The head or neck, back of the torso, arm and front of the torso are involved; no constitutional symptoms were reported; the patient considered this skin that appeared healthy to them; the contributor notes itching; the condition has been present for less than one week; close-up view.
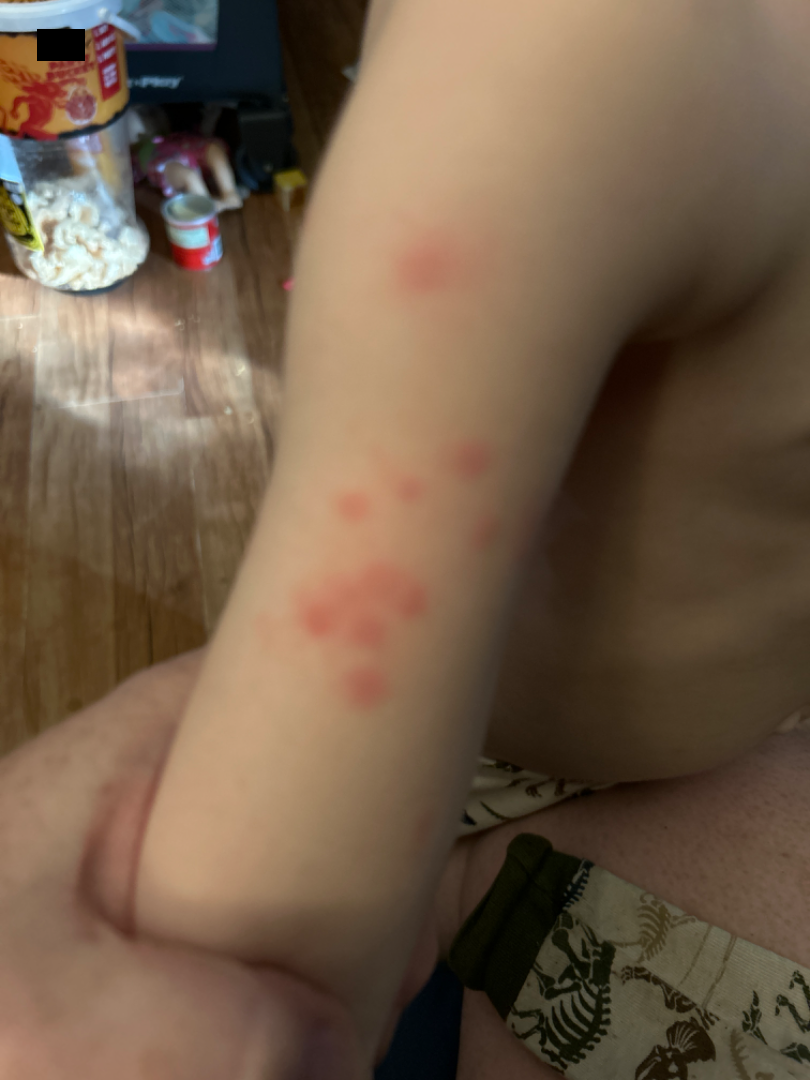{"assessment": "unable to determine"}